Symptoms reported: enlargement and itching · no associated systemic symptoms reported · the patient considered this a rash · located on the arm · the photograph was taken at an angle — 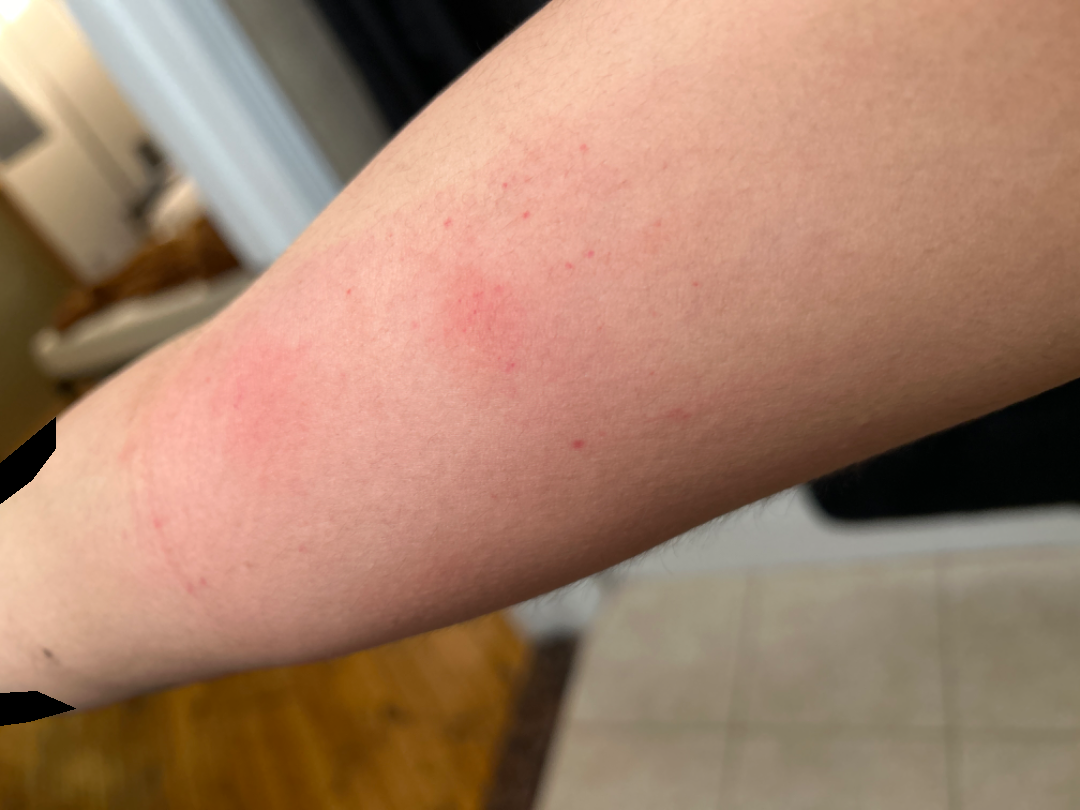<case>
  <differential>
    <leading>Insect Bite</leading>
    <considered>Deep fungal infection</considered>
    <unlikely>panniculitis of skin</unlikely>
  </differential>
</case>